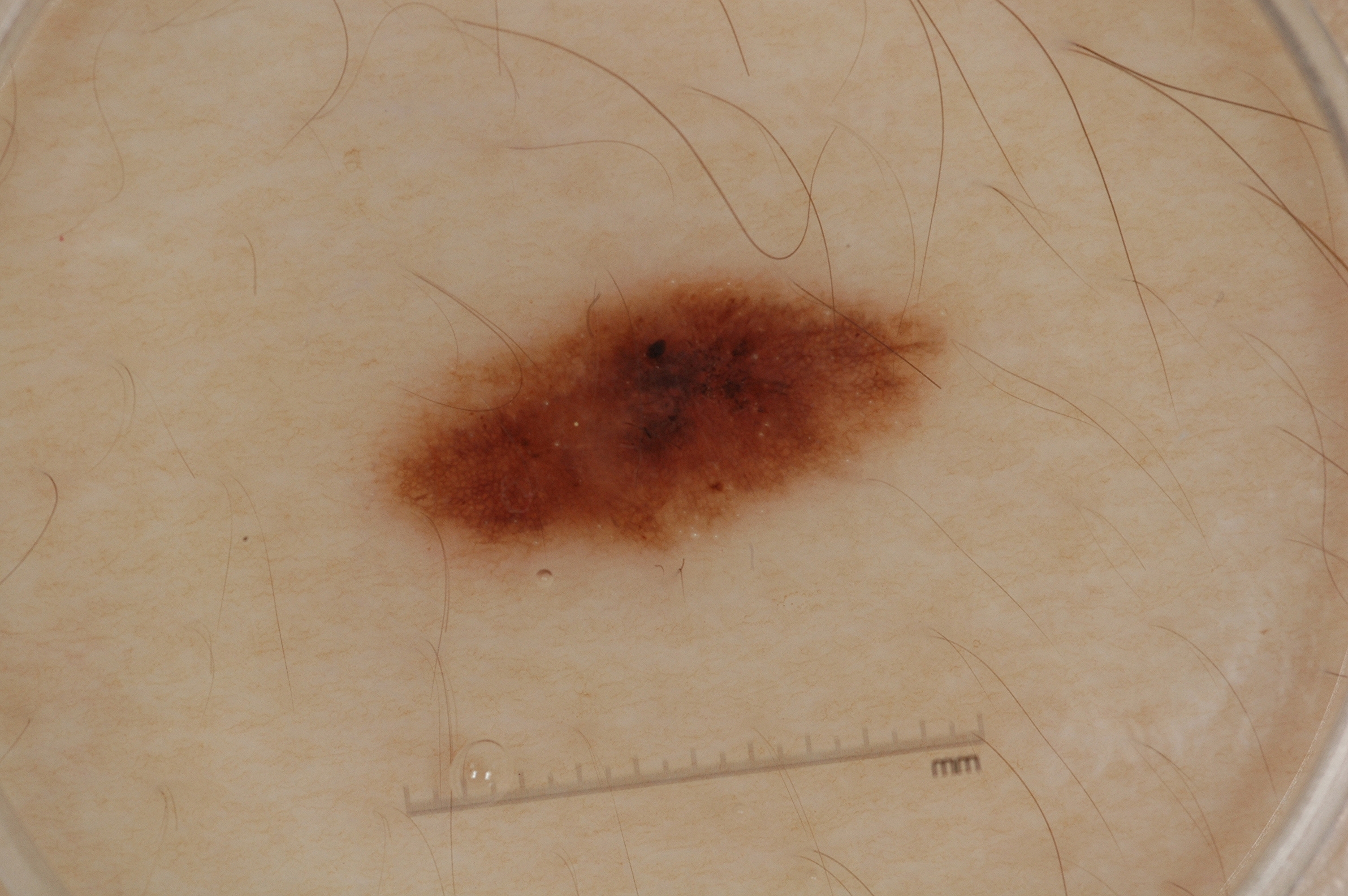patient — male, in their mid- to late 40s | modality — dermoscopy | dermoscopic pattern — milia-like cysts and pigment network; absent: negative network and streaks | bounding box — bbox=[379, 273, 948, 567] | impression — a melanocytic nevus, a benign skin lesion.